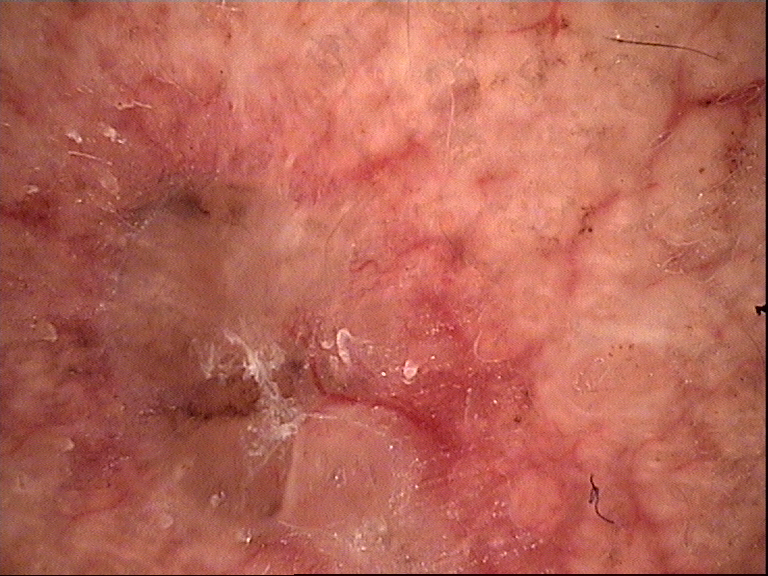diagnostic label — basal cell carcinoma (biopsy-proven).